A clinical close-up photograph of a skin lesion; recorded as Fitzpatrick skin type II; history notes alcohol use, prior malignancy (patient or family), and no tobacco use.
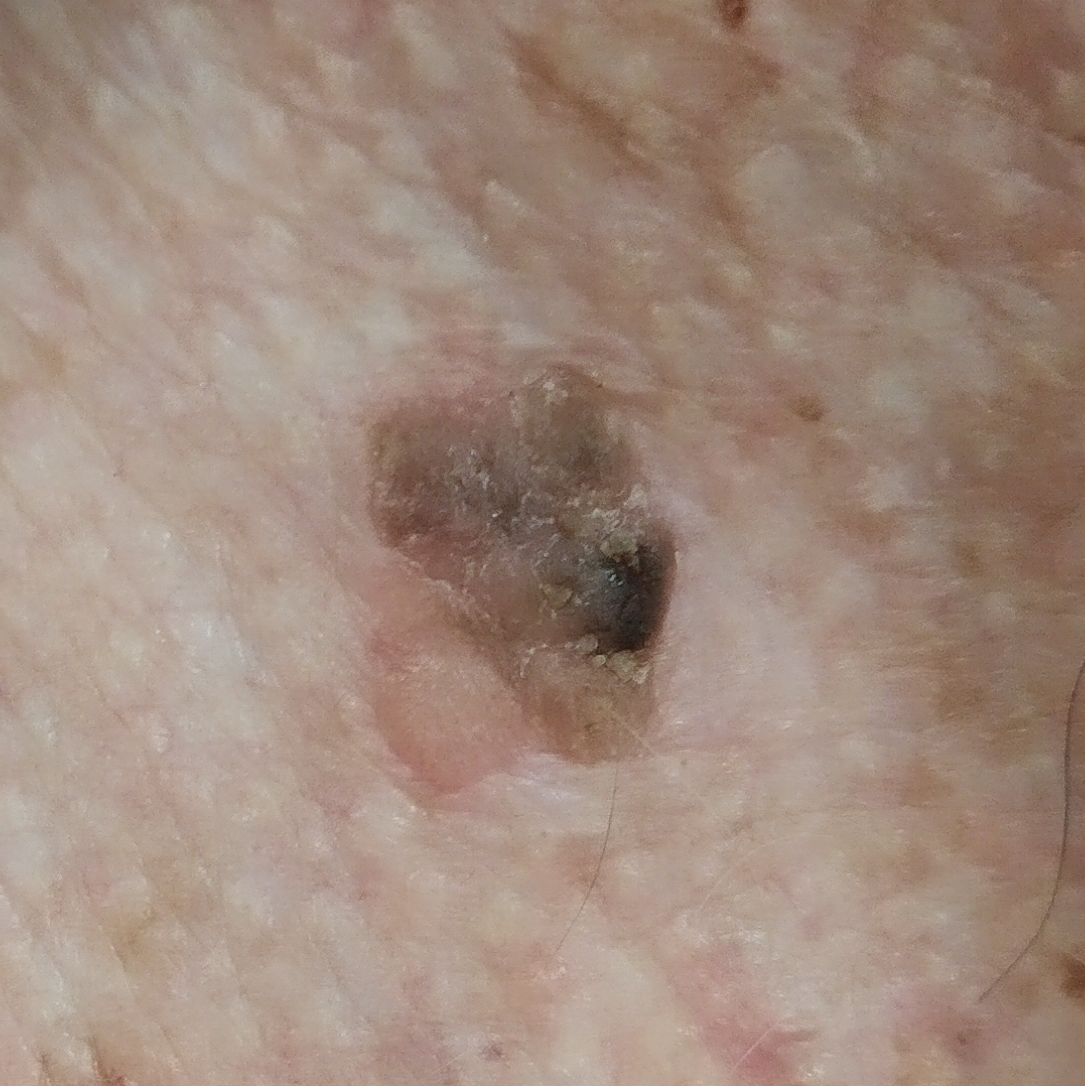The lesion measures approximately 12 × 11 mm.
Consistent with a benign lesion — a seborrheic keratosis.